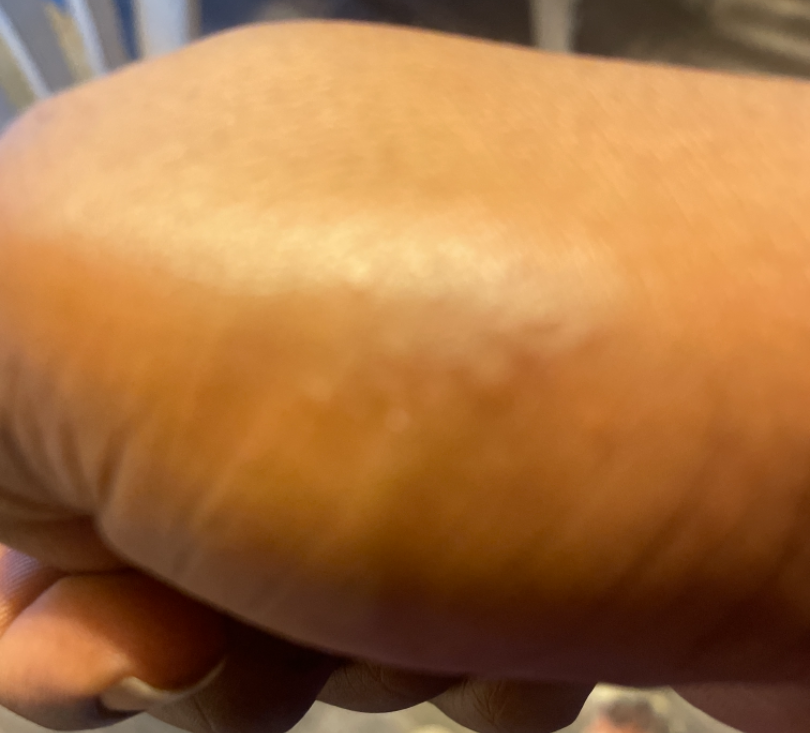The reviewing dermatologist was unable to assign a differential diagnosis from the image.